The patient says their skin reddens with sun exposure.
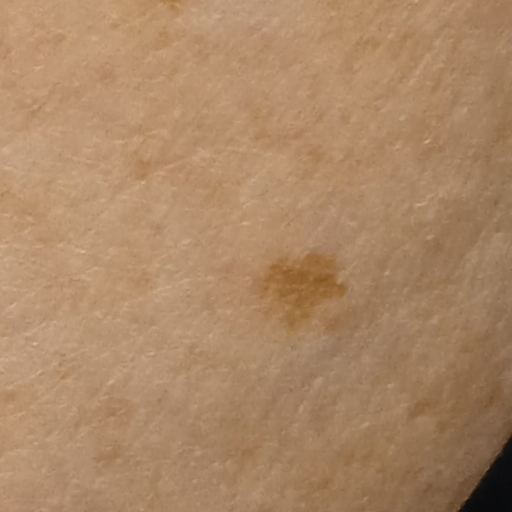The lesion is about 6.1 mm across. The consensus diagnosis for this lesion was a melanocytic nevus.